Collected as part of a research study, without a referral diagnosis; a female subject age 73; the patient describes having few moles overall; a dermatoscopic image of a skin lesion; the patient says their skin reddens with sun exposure:
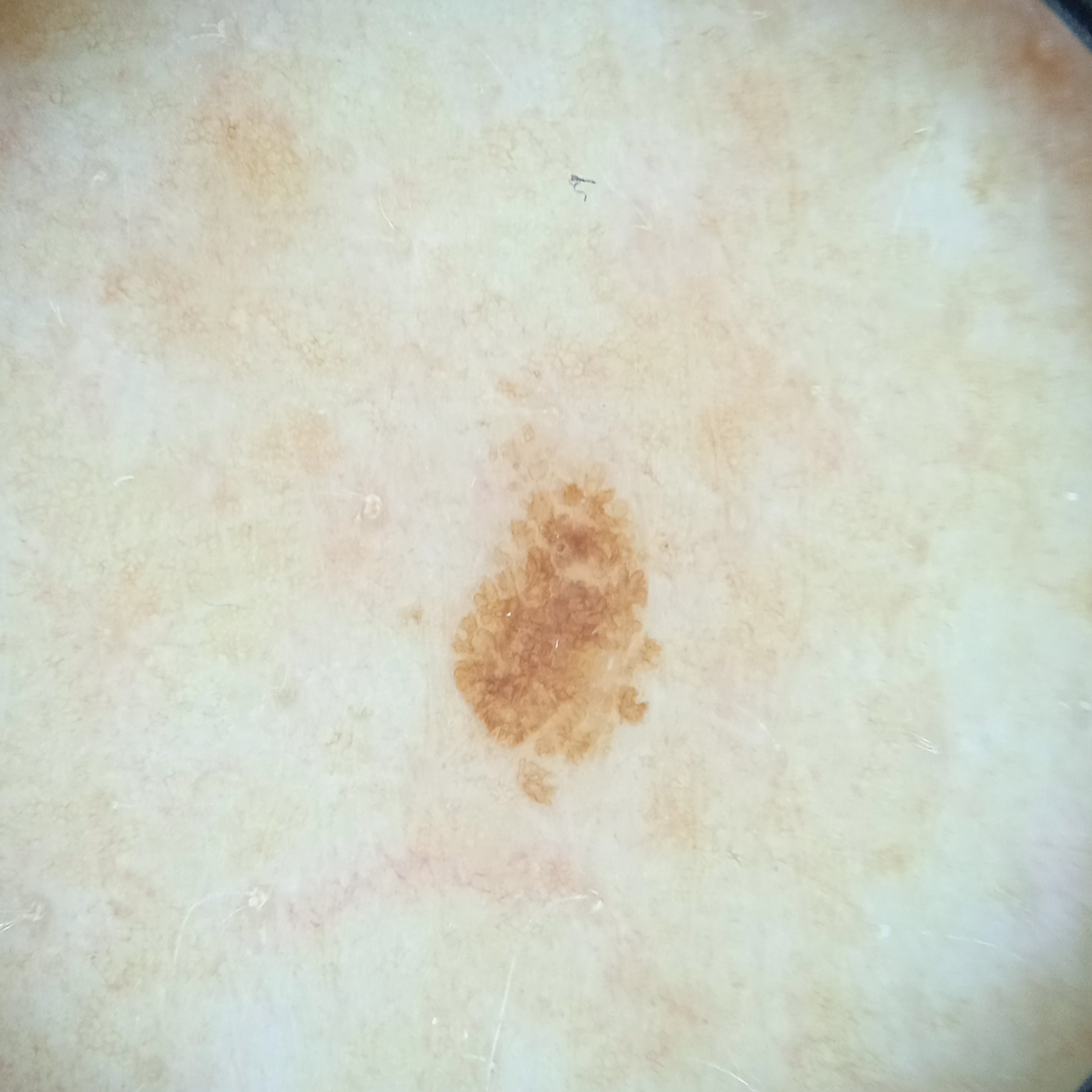* site — the back
* lesion size — 3.9 mm
* diagnosis — seborrheic keratosis (dermatologist consensus)